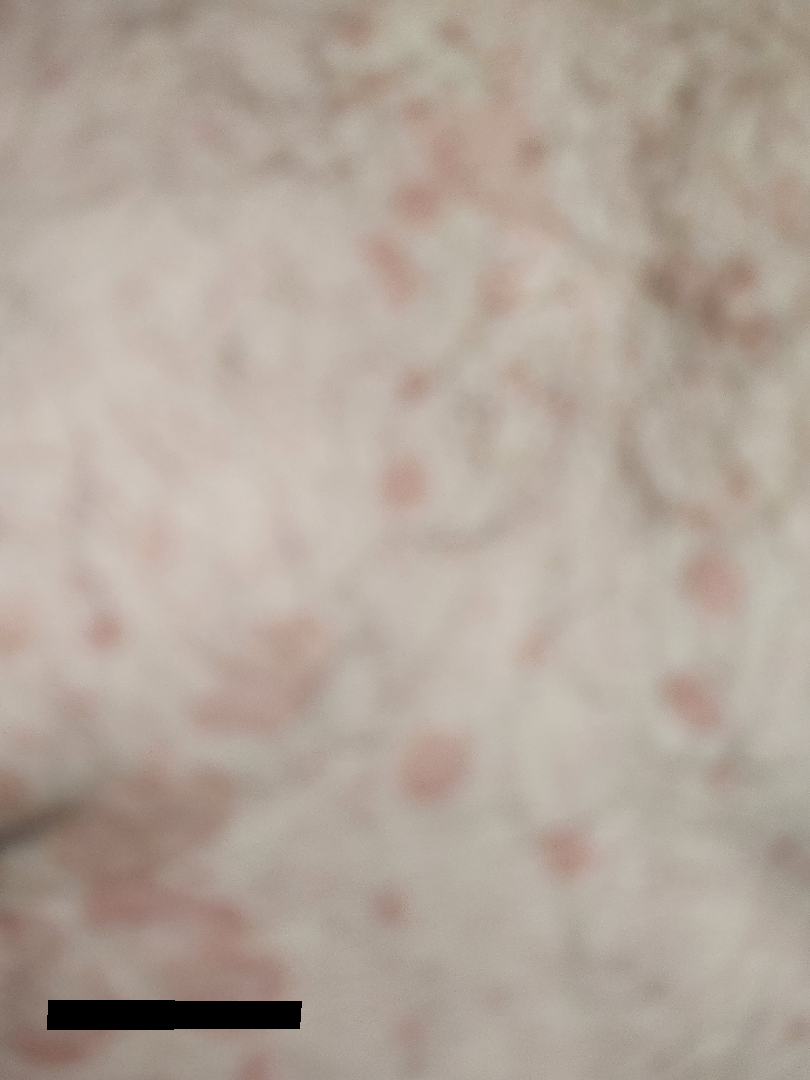Diagnostic features were not clearly distinguishable in this photograph.